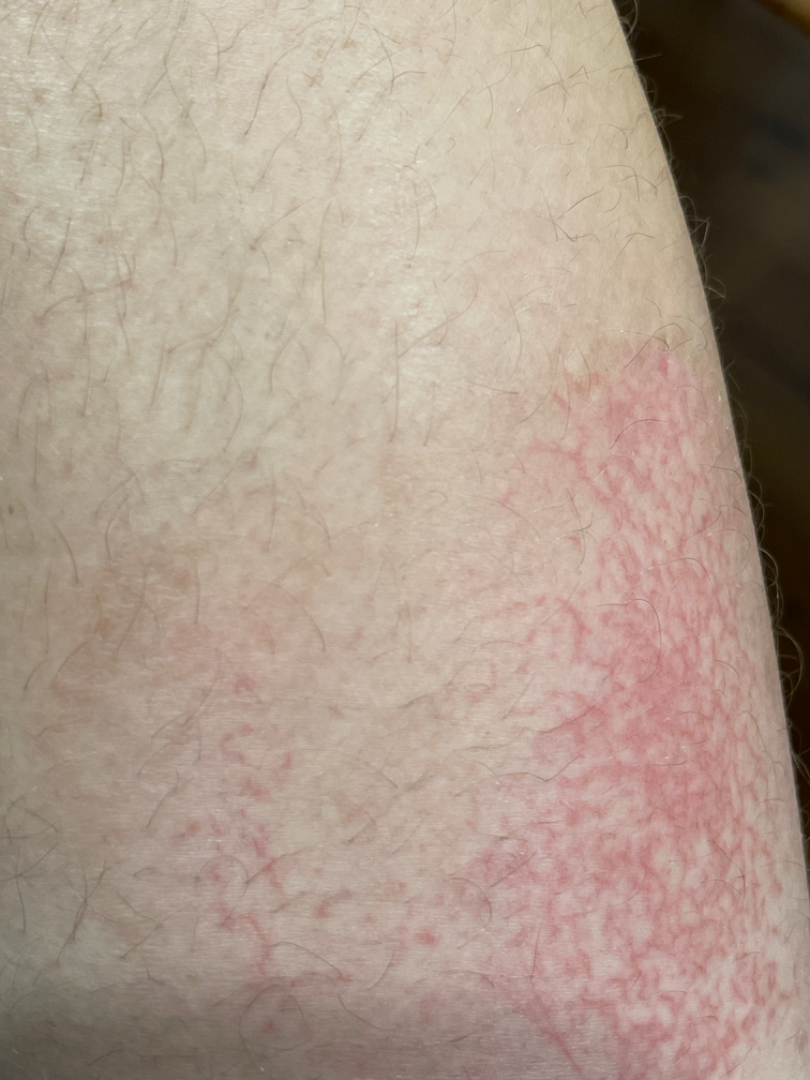Case summary:
- assessment · the leading impression is Eczema